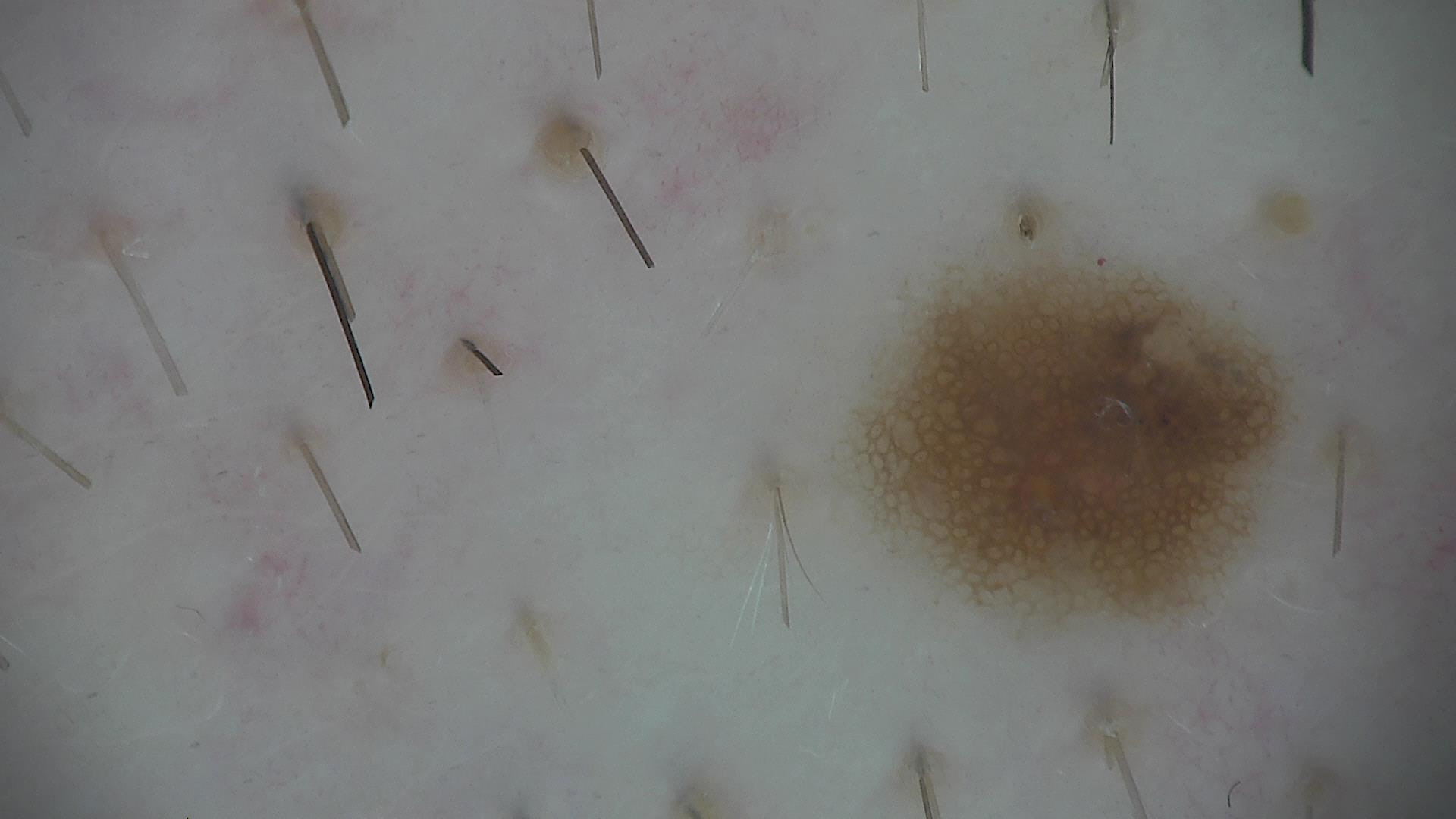label: dysplastic junctional nevus (expert consensus)